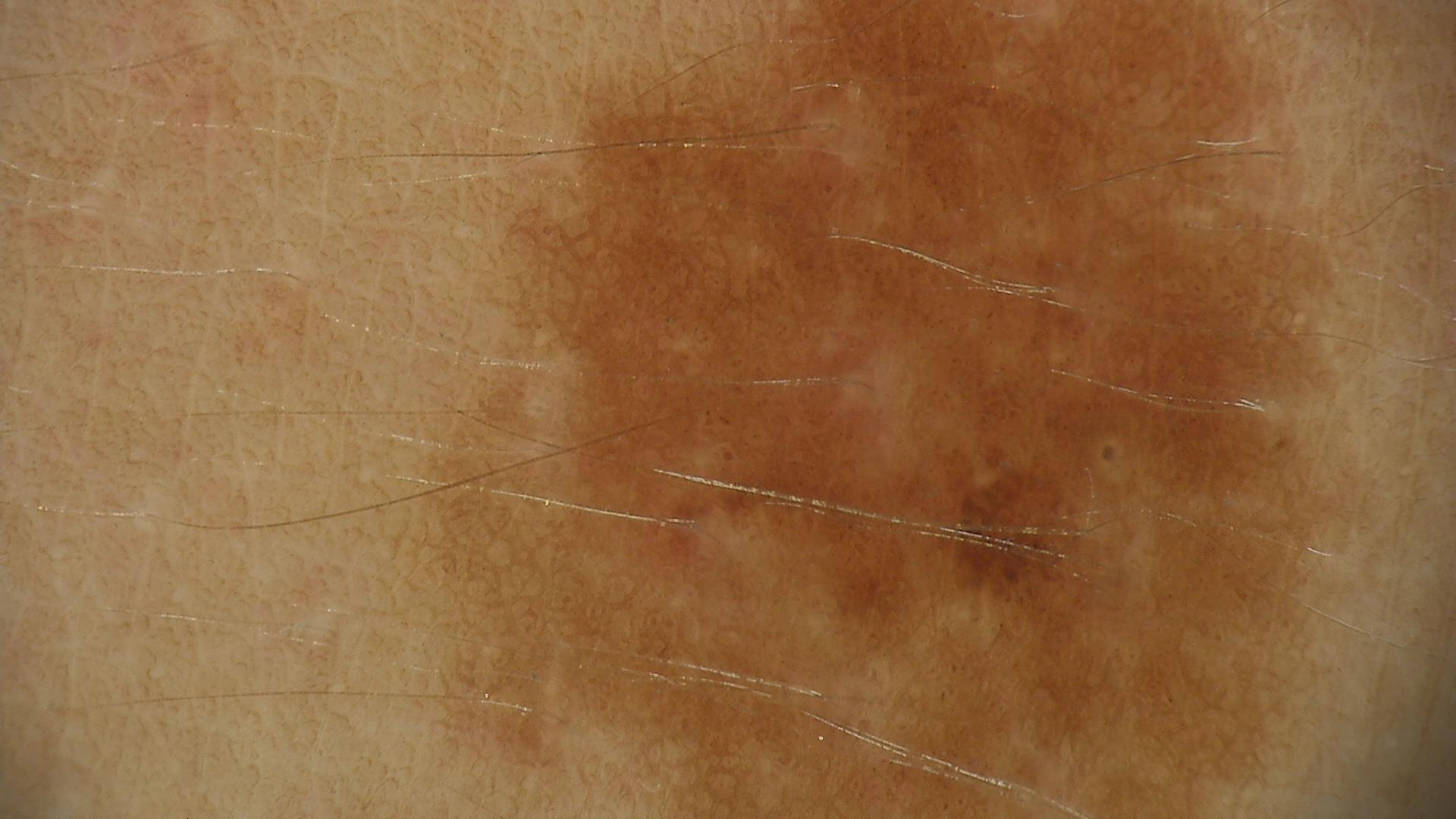Classified as a dysplastic junctional nevus.